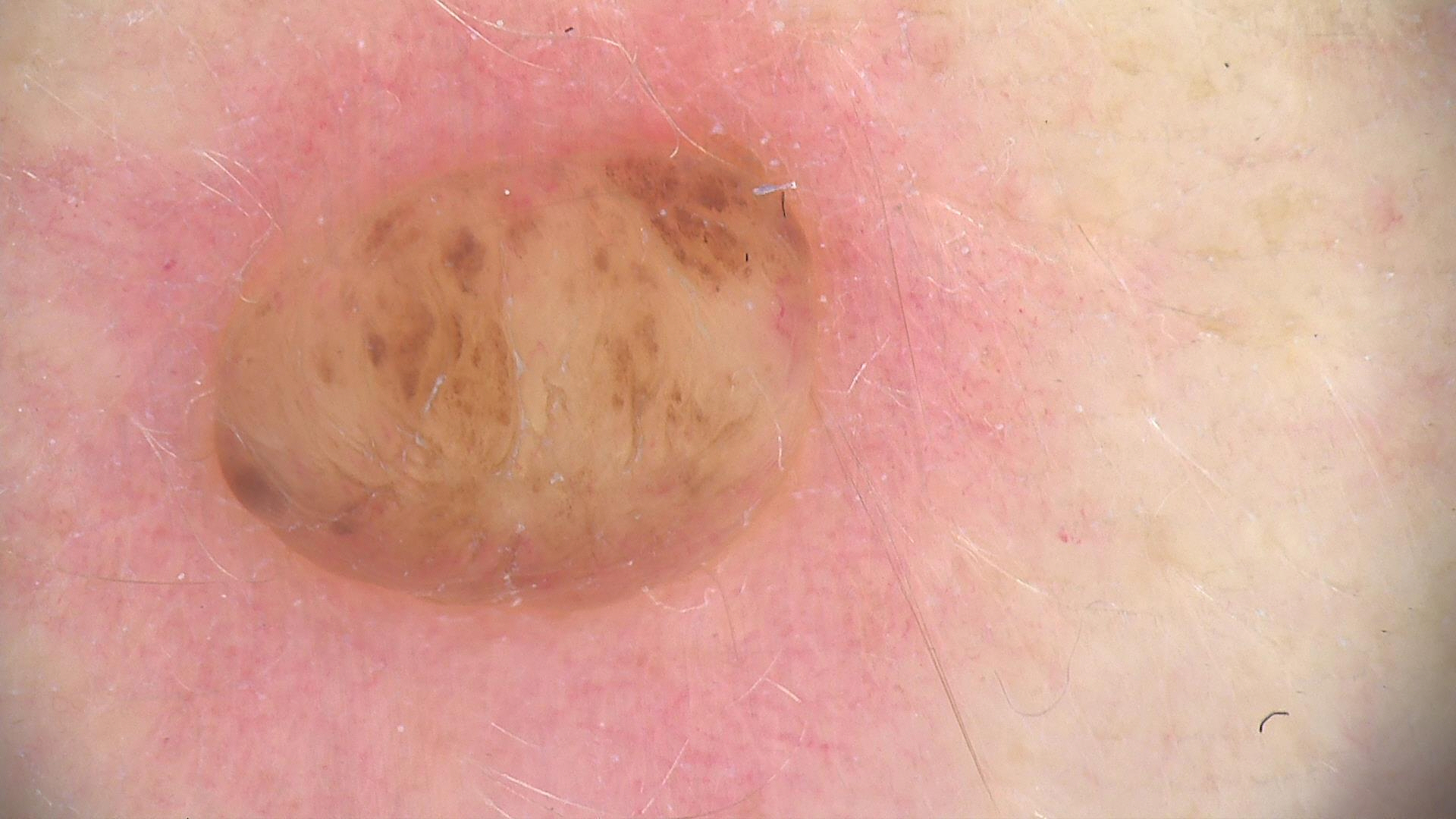Q: What is the diagnosis?
A: dermal nevus (expert consensus)